A dermatoscopic image of a skin lesion.
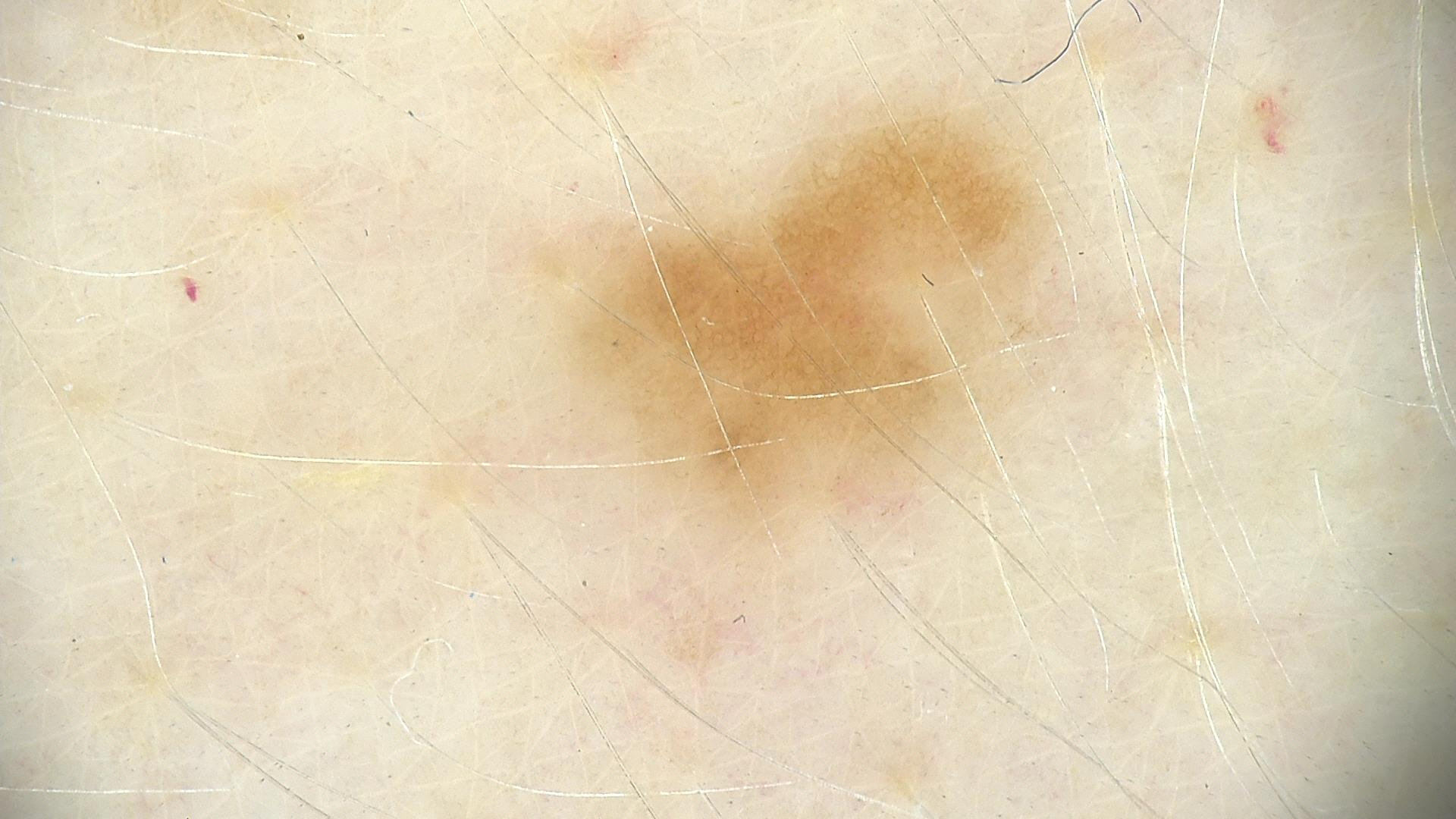Case:
- assessment · junctional nevus (expert consensus)